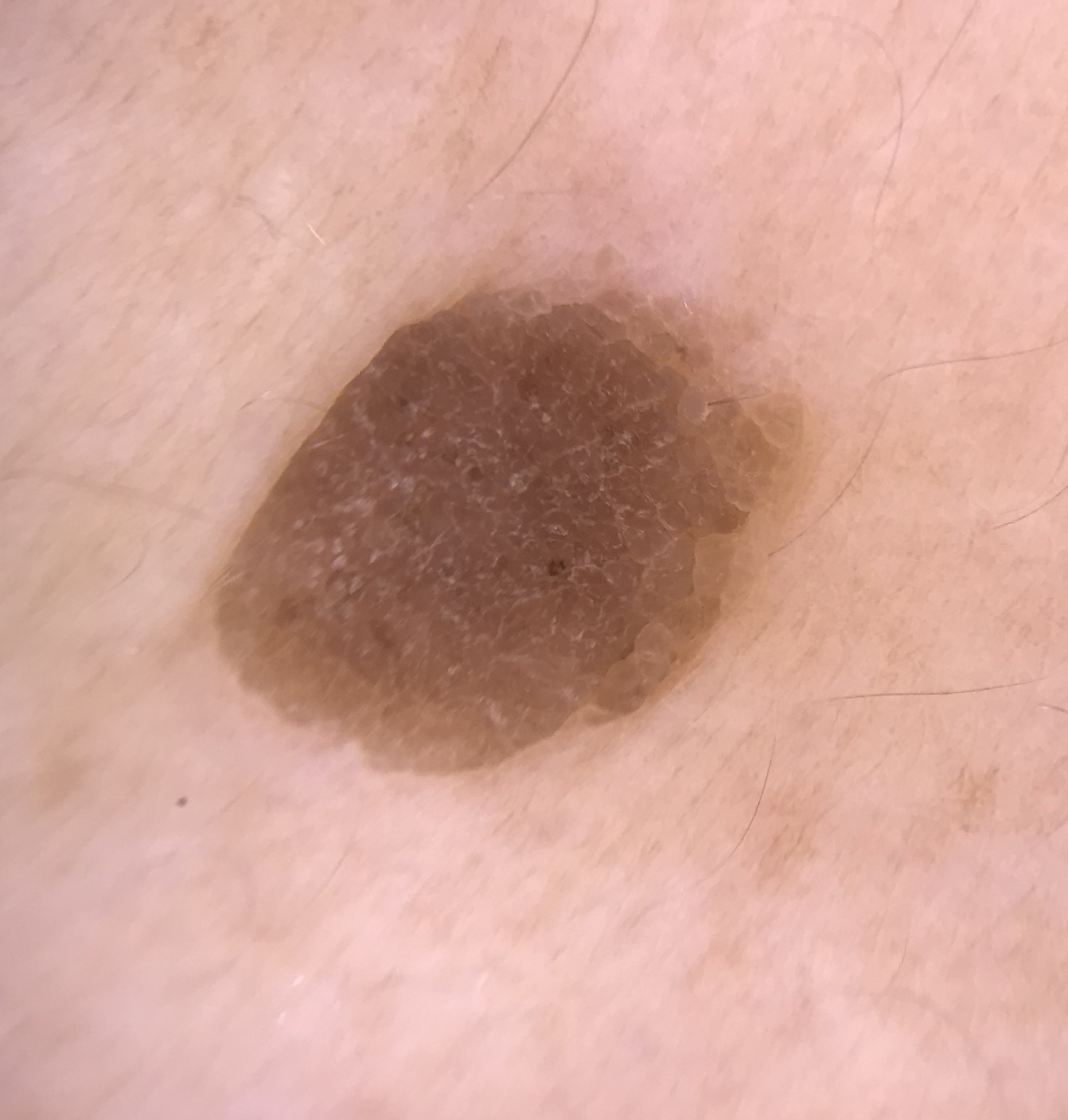image: dermoscopy
lesion_type:
  main_class: keratinocytic
diagnosis:
  name: seborrheic keratosis
  code: sk
  malignancy: benign
  super_class: non-melanocytic
  confirmation: expert consensus